This is a dermoscopic photograph of a skin lesion.
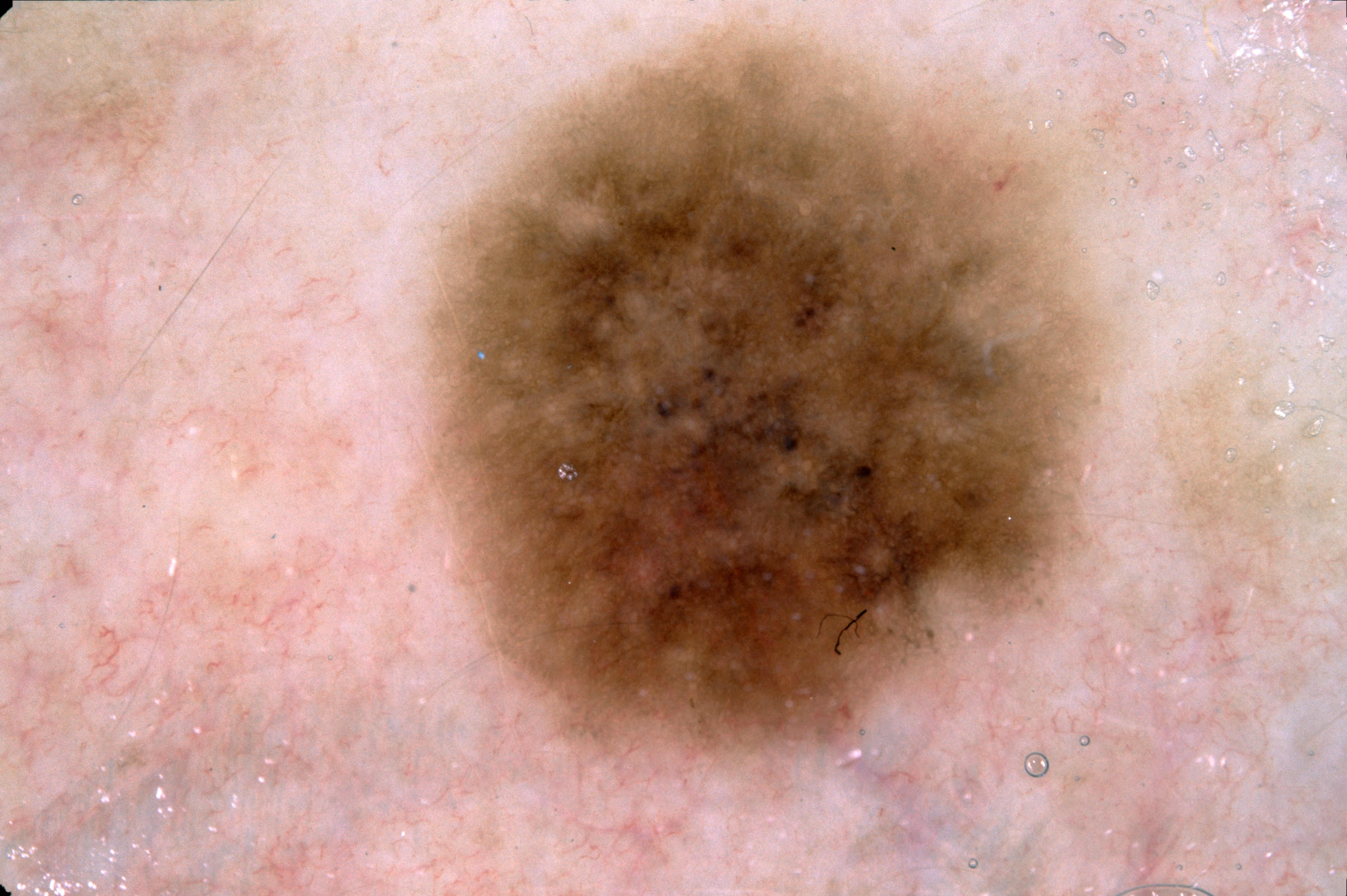<dermoscopy>
  <lesion_location>
    <bbox_xyxy>407, 13, 1135, 777</bbox_xyxy>
  </lesion_location>
  <diagnosis>
    <name>melanocytic nevus</name>
    <malignancy>benign</malignancy>
    <lineage>melanocytic</lineage>
    <provenance>clinical</provenance>
  </diagnosis>
</dermoscopy>